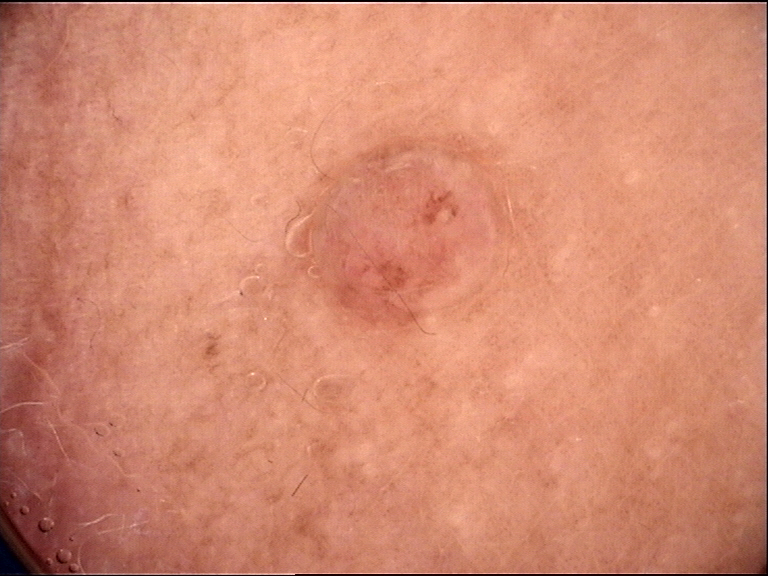This is a banal lesion. Consistent with a dermal nevus.